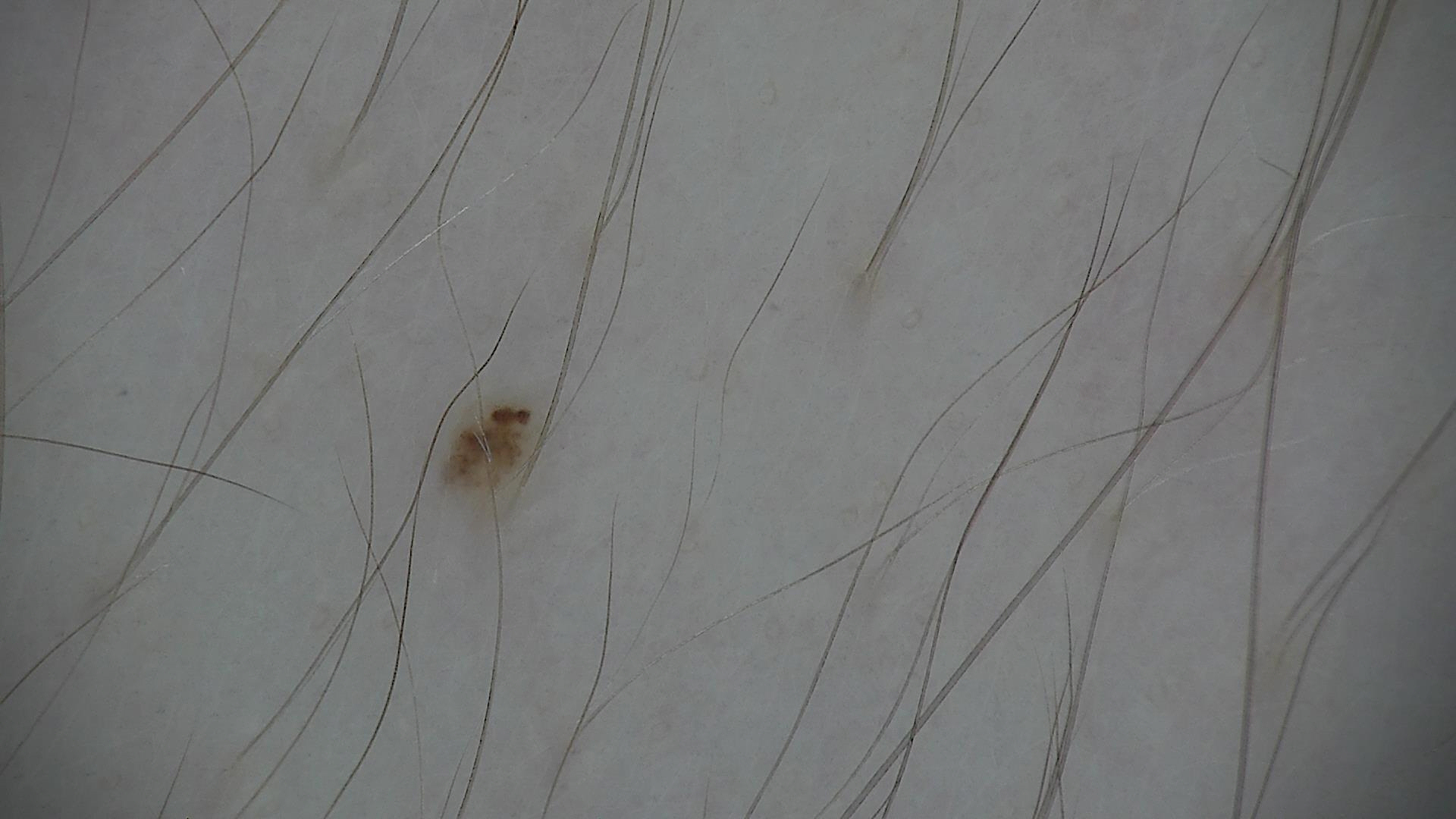diagnostic label = dysplastic junctional nevus (expert consensus).